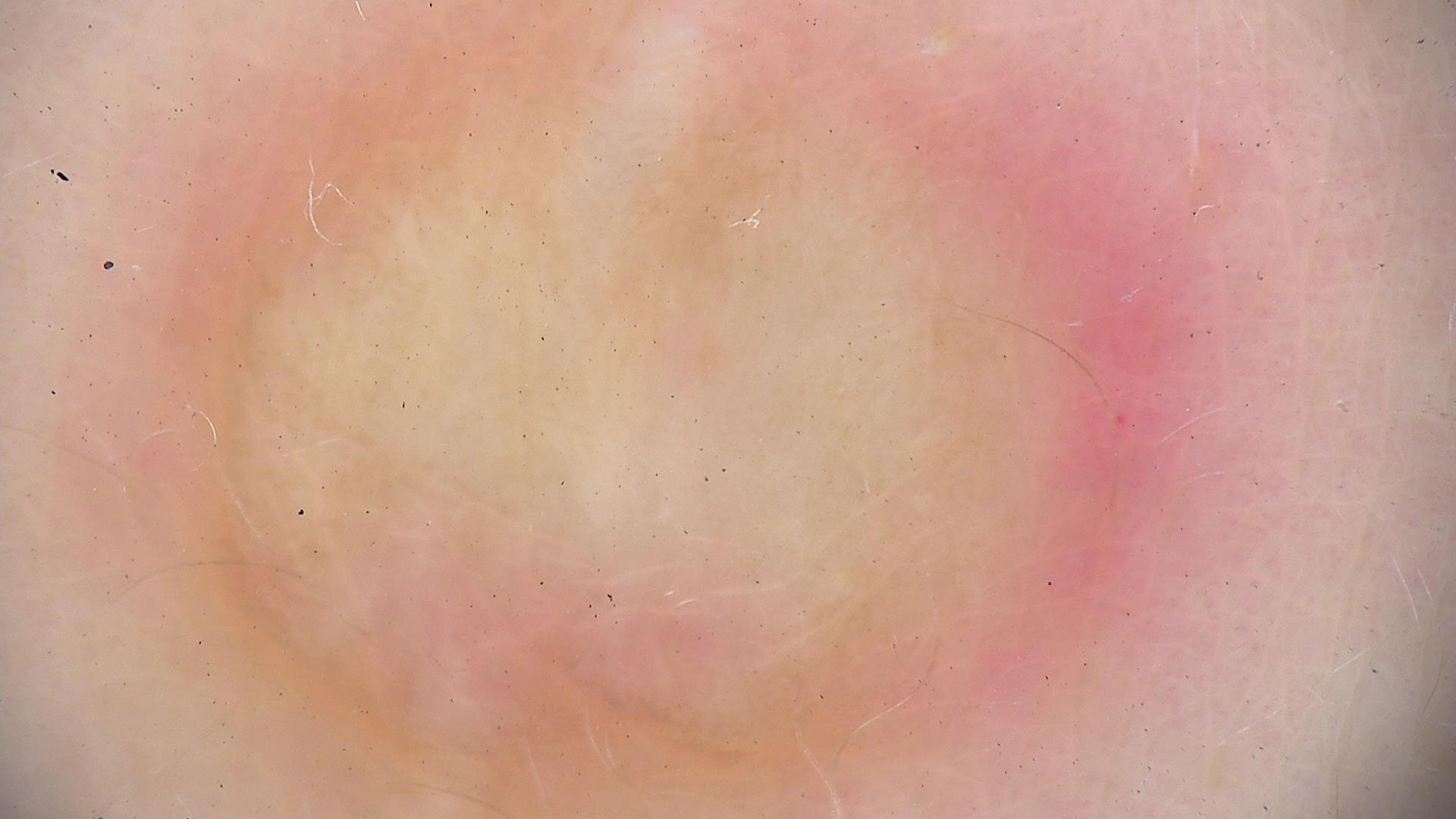The morphology is that of a fibro-histiocytic lesion. Classified as a dermatofibroma.